Dermoscopy of a skin lesion:
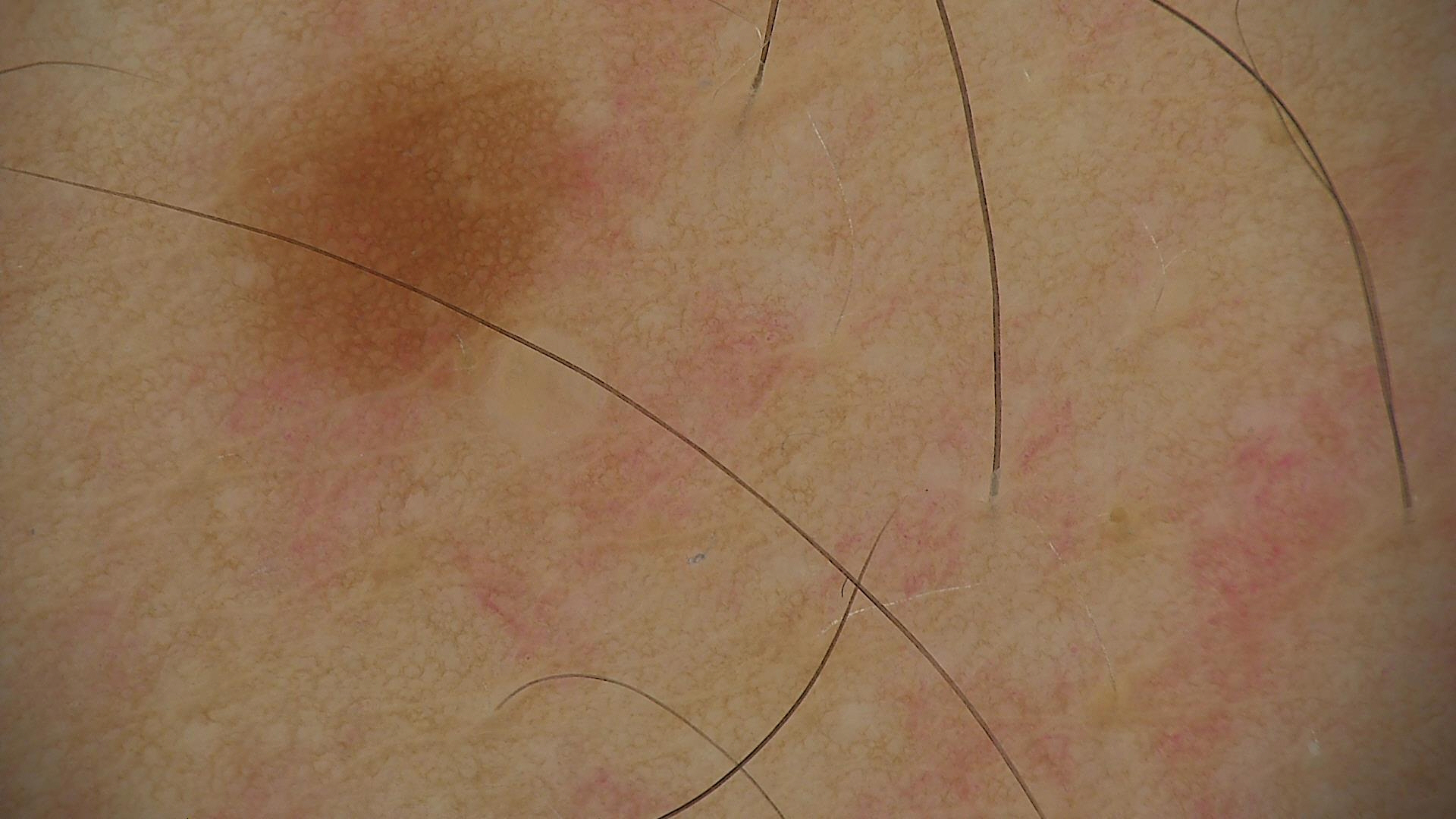– class · lentigo simplex (expert consensus)